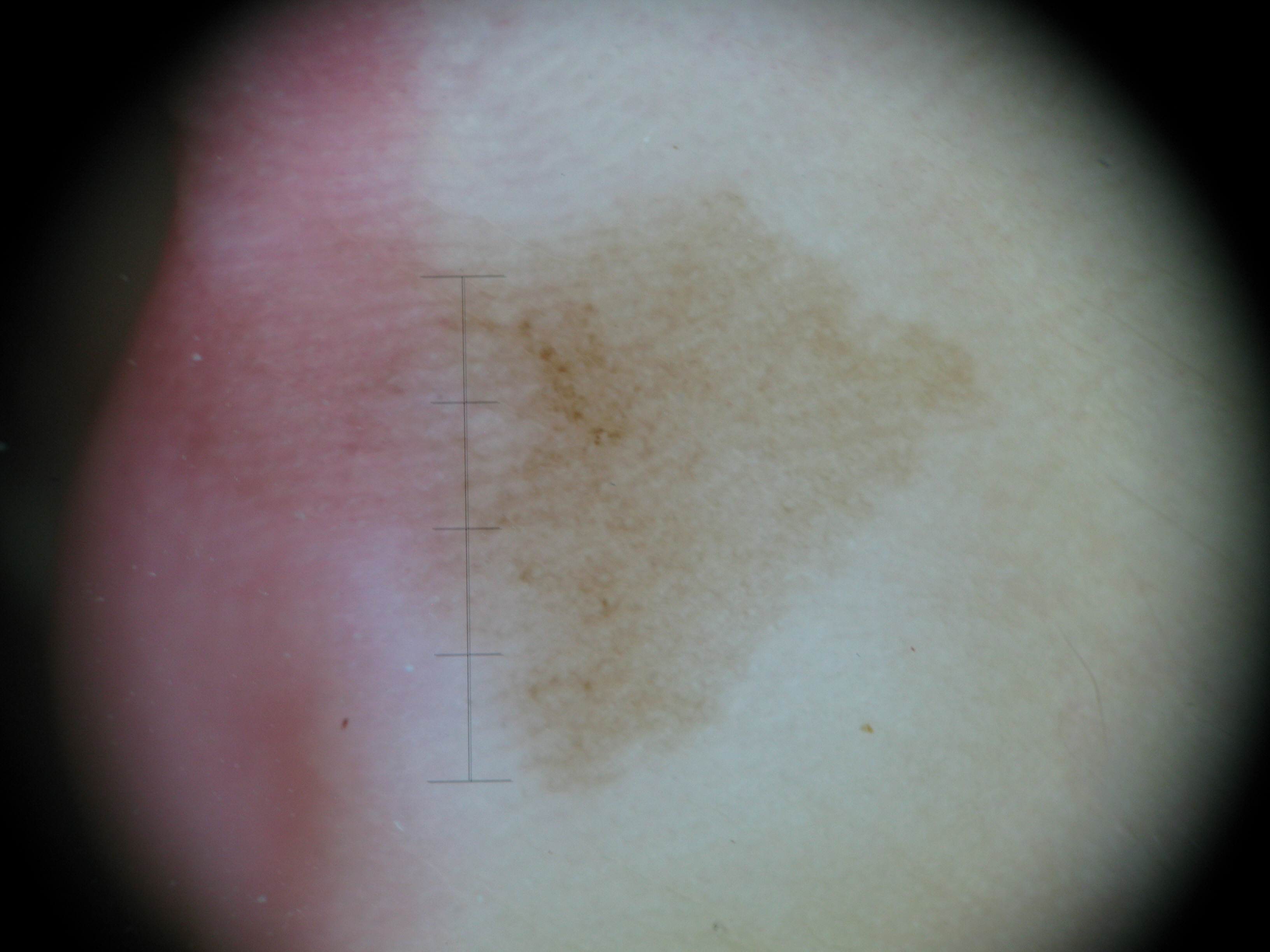Case:
- diagnosis: acral junctional nevus (expert consensus)